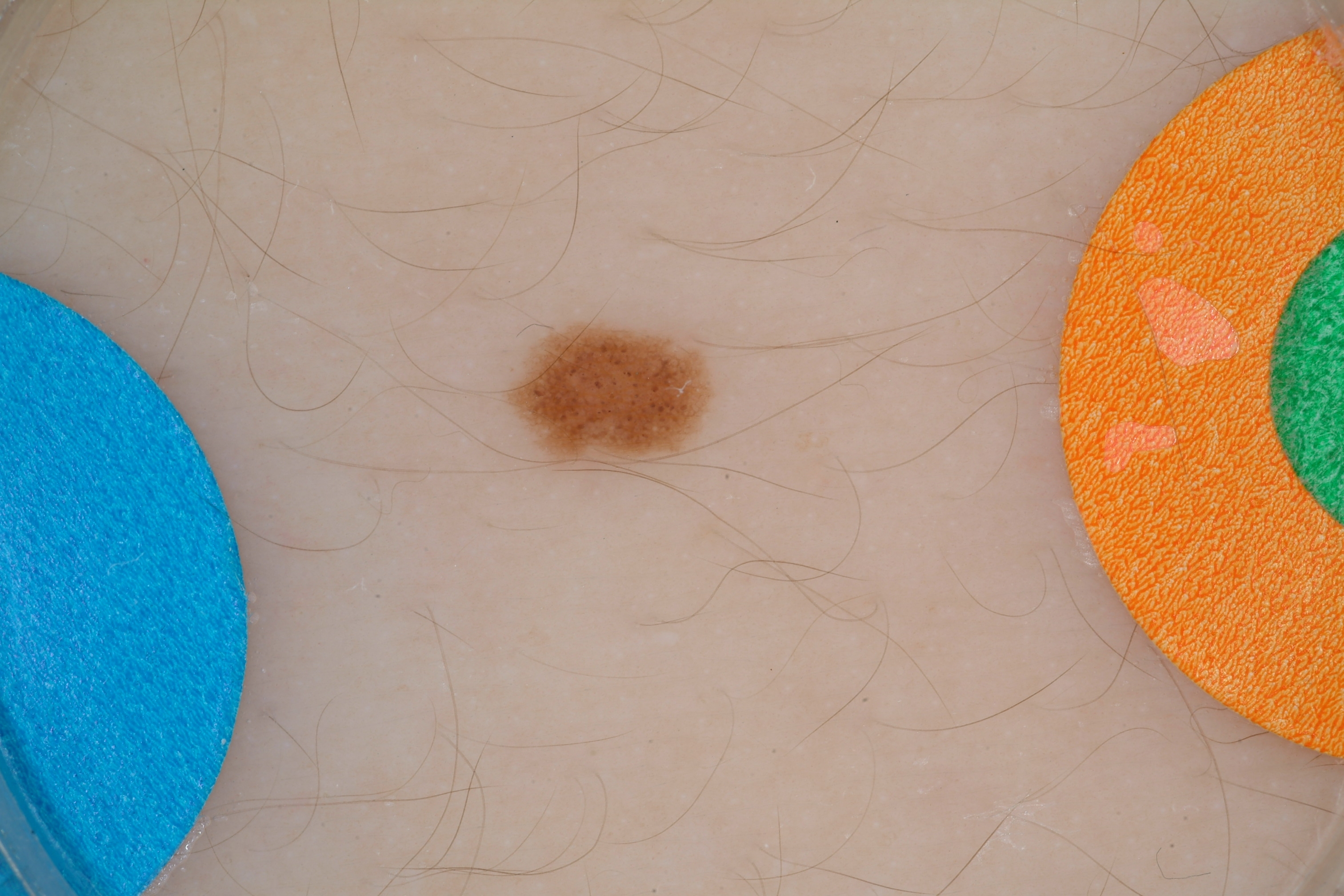| field | value |
|---|---|
| patient | female, aged 13 to 17 |
| image type | dermoscopic image |
| lesion bbox | 494/307/736/476 |
| features | pigment network; absent: milia-like cysts, streaks, and negative network |
| size | ~3% of the field |
| diagnostic label | a melanocytic nevus, a benign lesion |